The photograph is a close-up of the affected area. The leg is involved. The patient is 18–29, female: 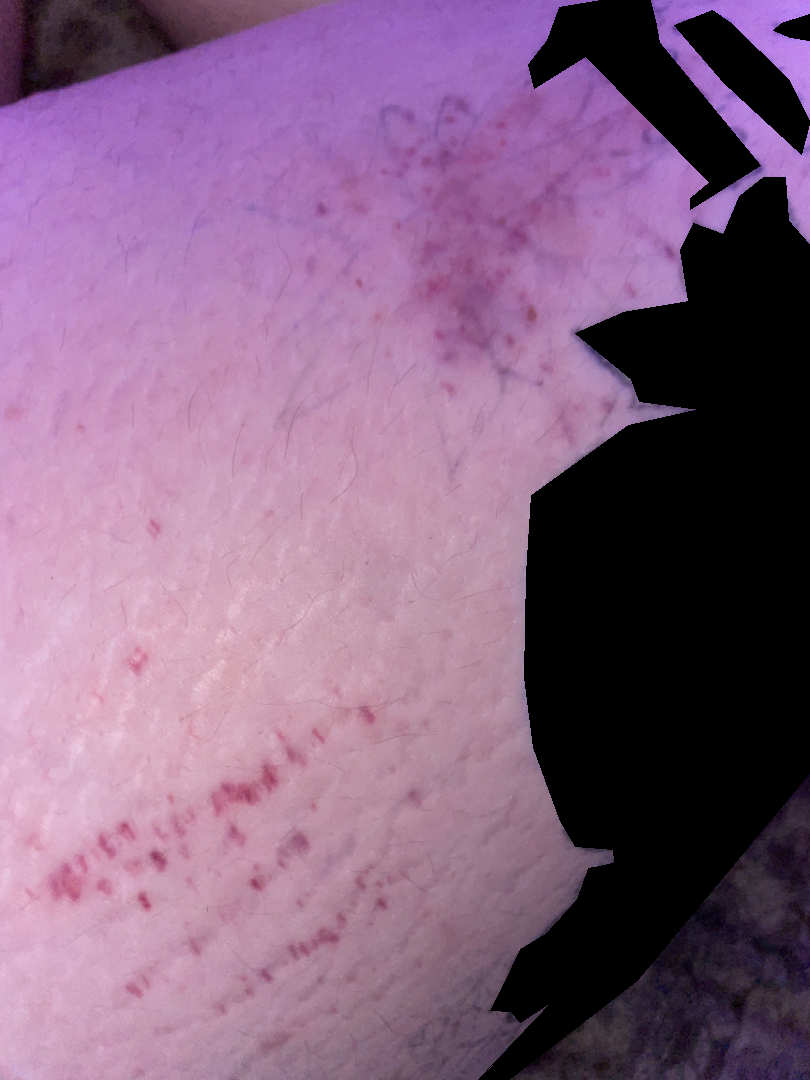assessment — indeterminate from the photograph